A male subject aged 76 · acquired for a research image collection, with no referral diagnosis · the patient says their skin reddens with sun exposure · a clinical photograph showing a skin lesion · by self-report, a personal history of skin cancer, a personal history of cancer, no family history of skin cancer, and no sunbed use — 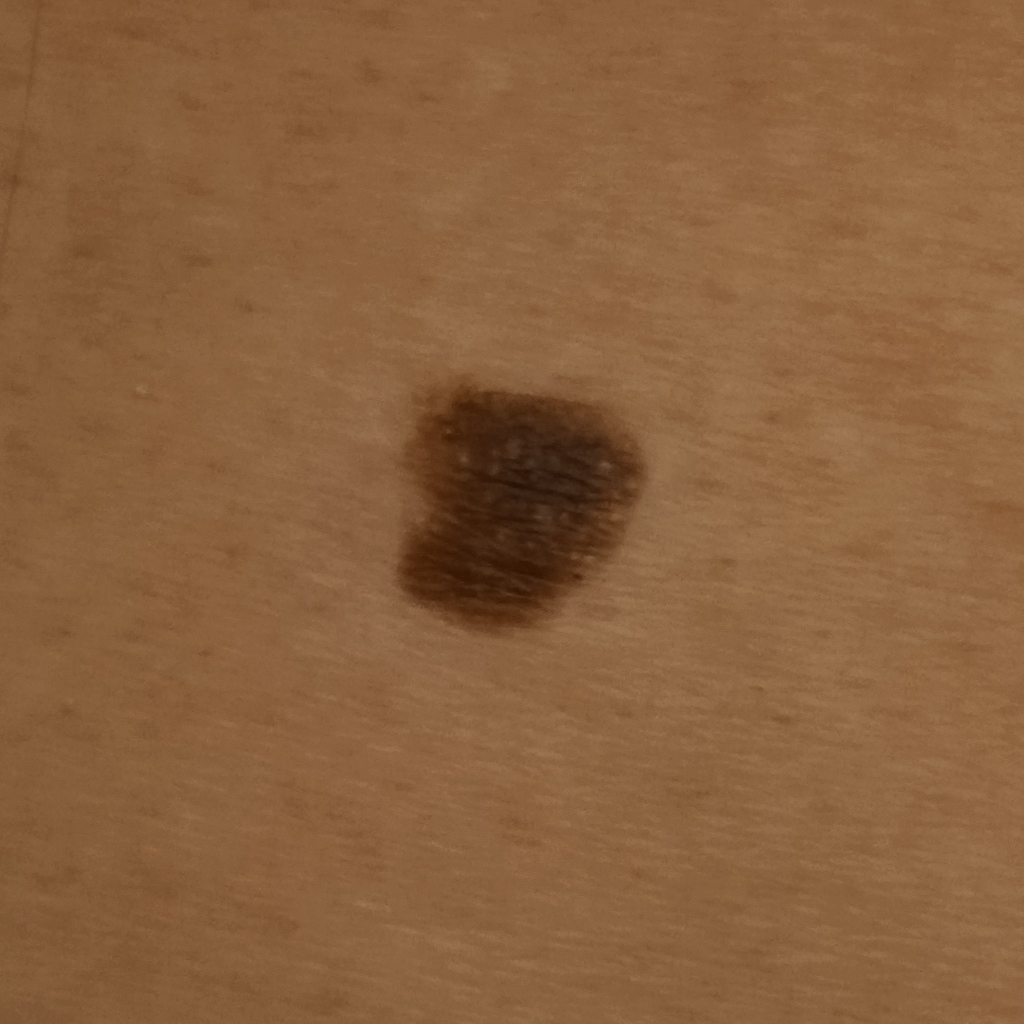| feature | finding |
|---|---|
| diagnosis | seborrheic keratosis (dermatologist consensus) |